The contributor notes the lesion is flat. Located on the leg. The contributor is a female aged 50–59. The photograph is a close-up of the affected area. The contributor notes bothersome appearance, itching and enlargement. Reported duration is about one day. The patient also reports mouth sores and fever. The patient described the issue as a rash.
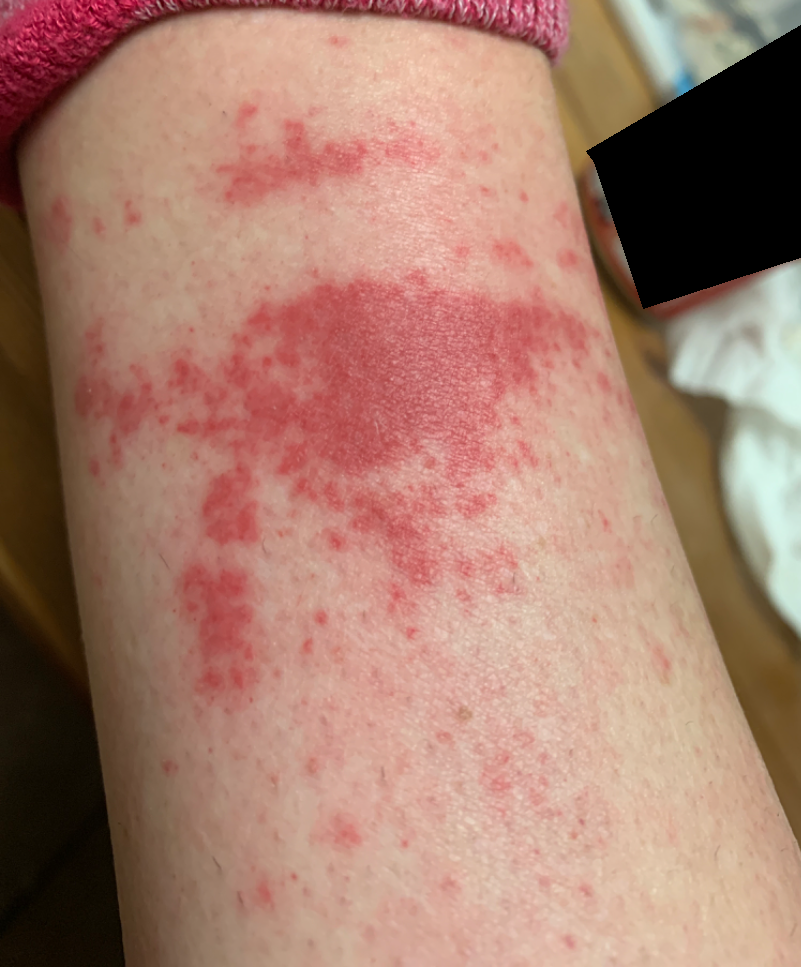differential = Stasis Dermatitis; Acute dermatitis, NOS; and Leukocytoclastic Vasculitis were each considered, in no particular order